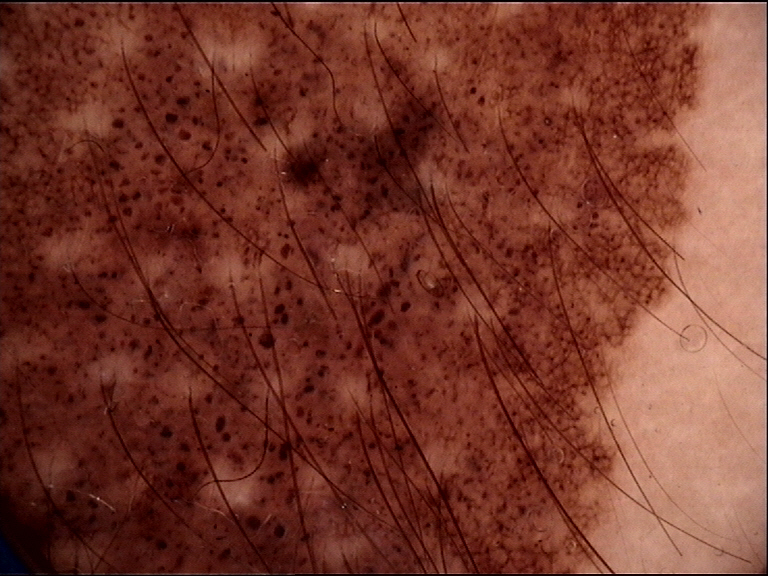subtype: banal | diagnostic label: congenital compound nevus (expert consensus).